The patient described the issue as a rash · symptoms reported: itching, enlargement and bothersome appearance · located on the arm and back of the hand · female contributor, age 18–29 · the contributor reports the condition has been present for one to four weeks · texture is reported as raised or bumpy · the photograph is a close-up of the affected area: 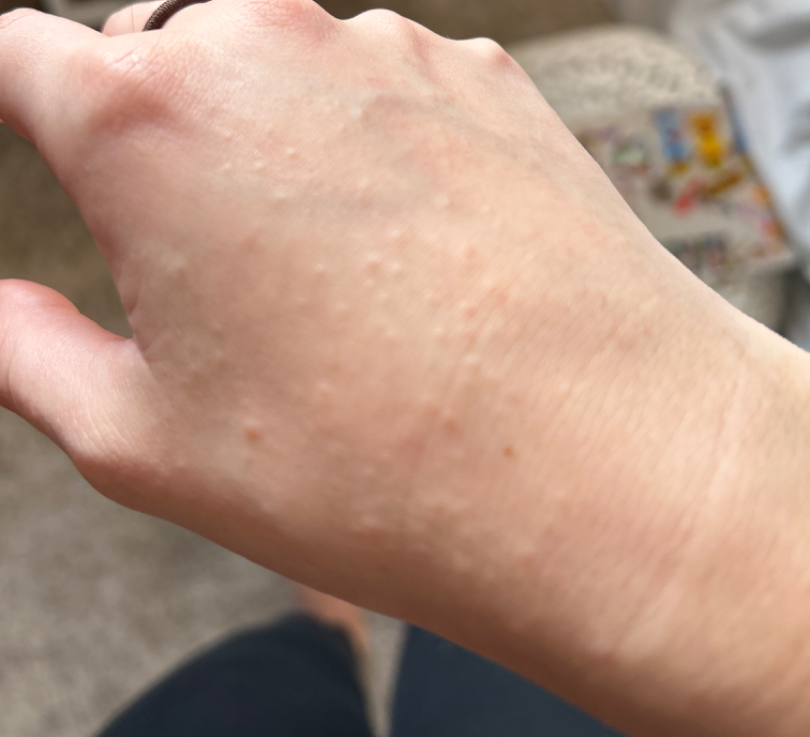assessment — most consistent with Lichen nitidus; the differential also includes Eczema.